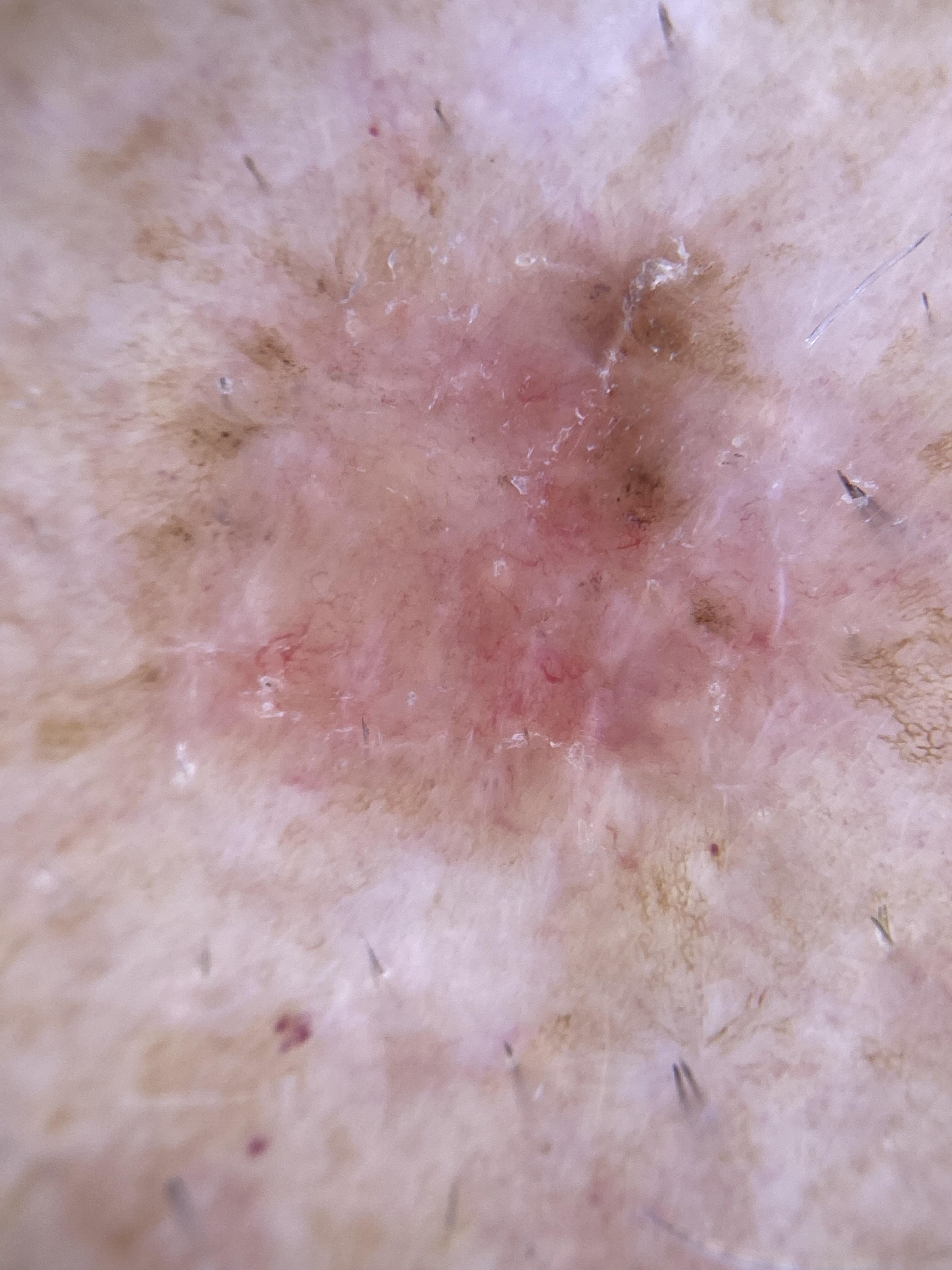patient=male, about 75 years old; FST=II; anatomic site=the trunk (the anterior trunk); diagnostic label=Basal cell carcinoma (biopsy-proven).